A dermoscopy image of a single skin lesion: 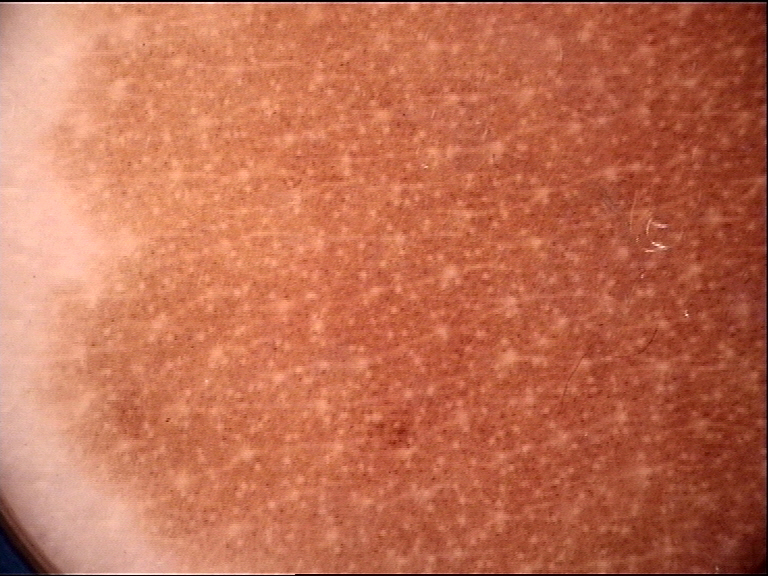The morphology is that of a banal lesion. Labeled as a congenital compound nevus.